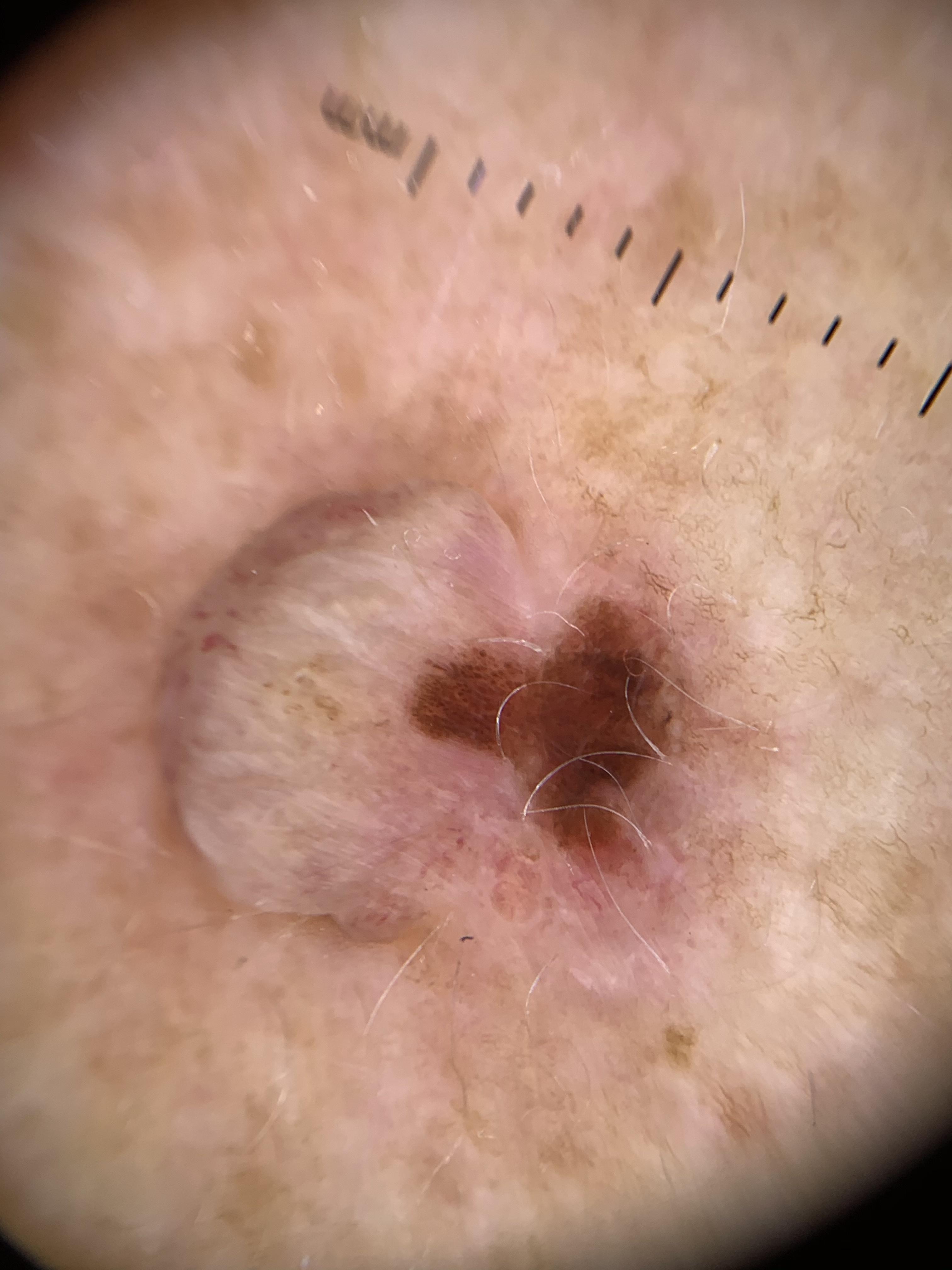{
  "diagnosis": {
    "name": "Nevus",
    "malignancy": "benign",
    "confirmation": "histopathology",
    "lineage": "melanocytic"
  }
}